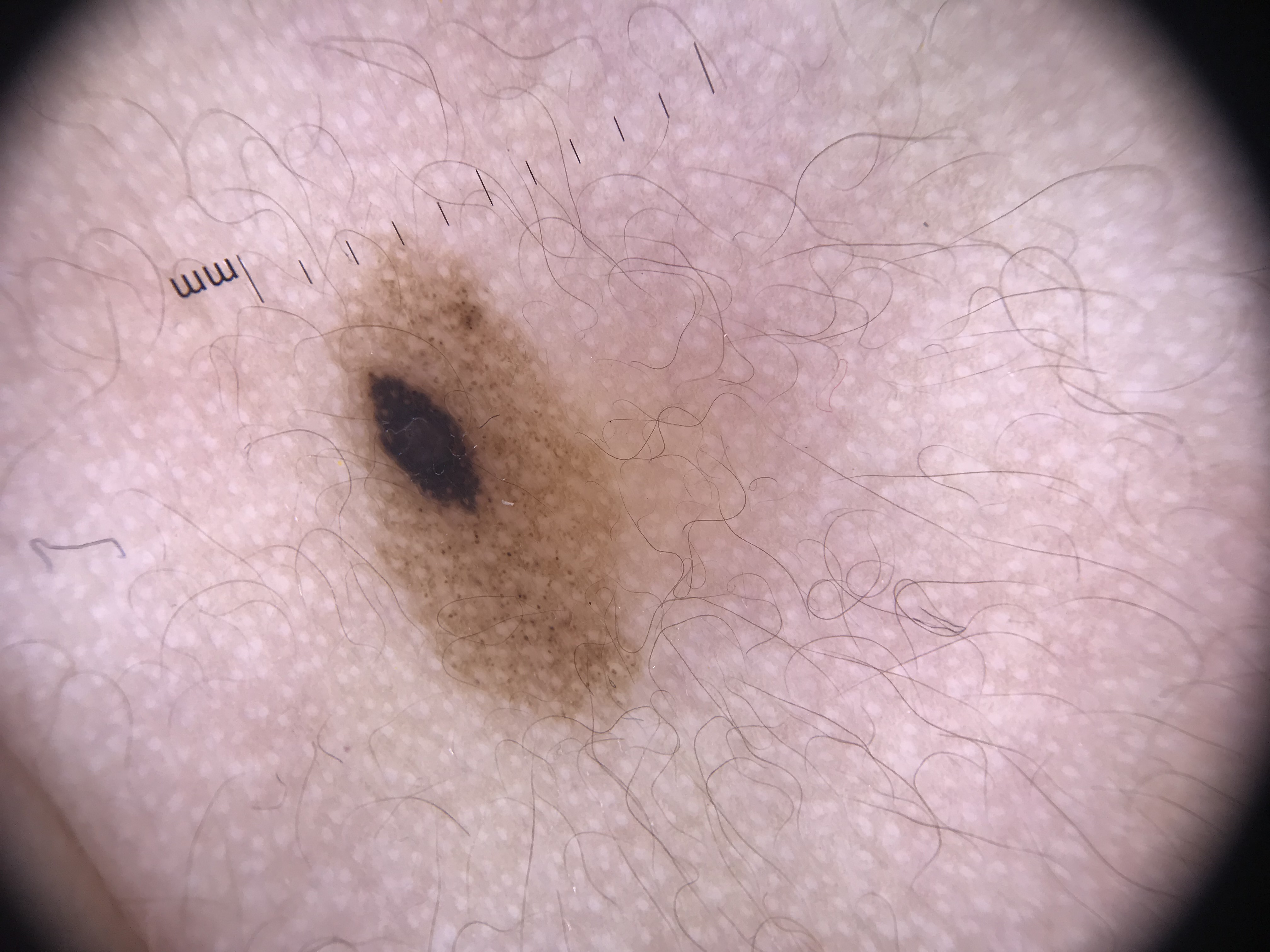The architecture is that of a banal lesion.
Labeled as a congenital compound nevus.